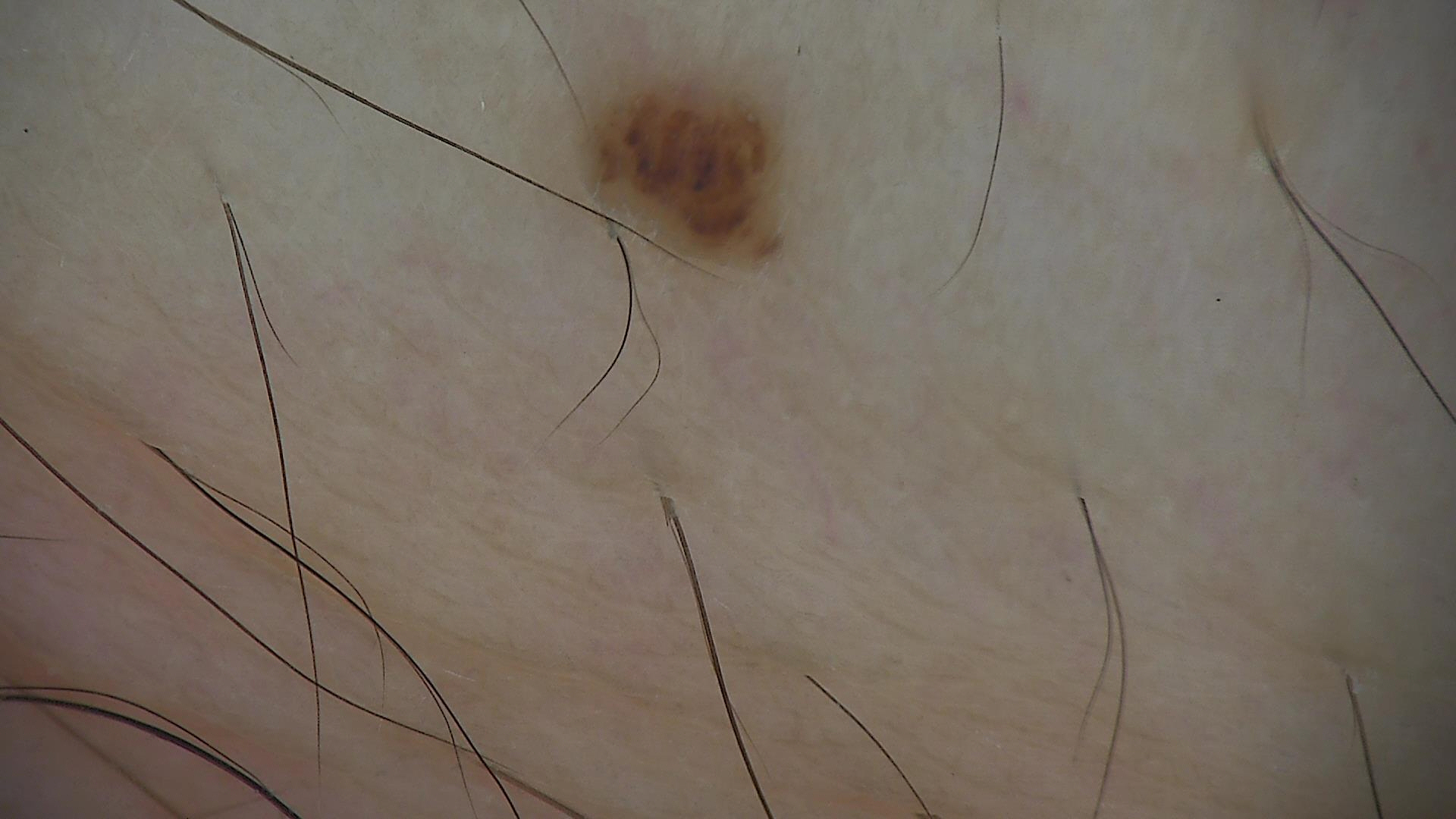Labeled as a dysplastic junctional nevus.